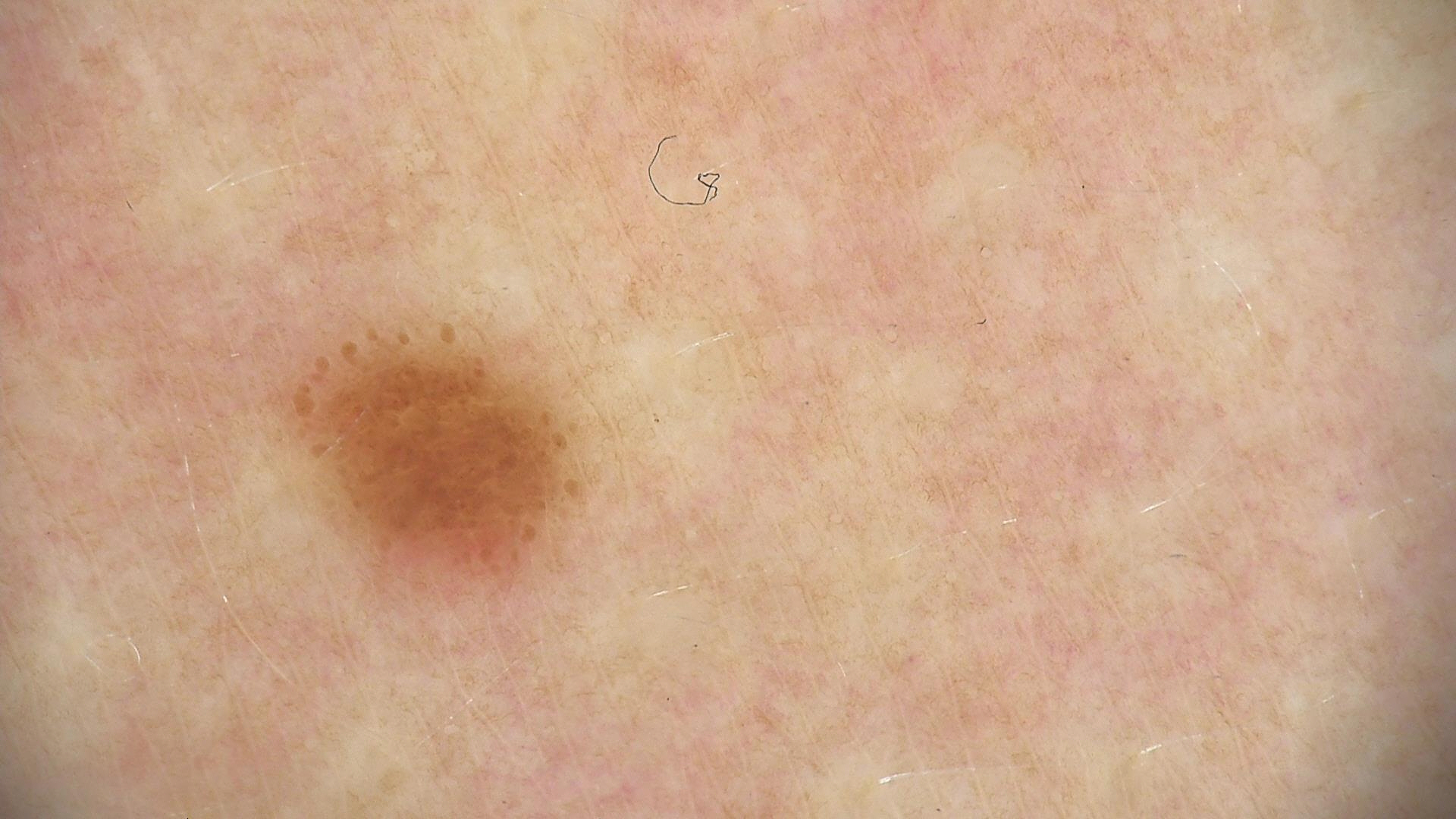<dermoscopy>
  <diagnosis>
    <name>dysplastic junctional nevus</name>
    <code>jd</code>
    <malignancy>benign</malignancy>
    <super_class>melanocytic</super_class>
    <confirmation>expert consensus</confirmation>
  </diagnosis>
</dermoscopy>